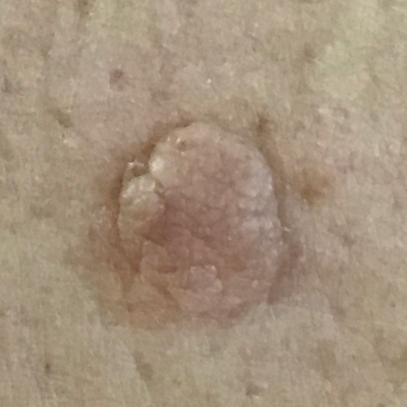imaging: smartphone clinical photo | subject: 61 years old | region: the back | reported symptoms: elevation / no itching, no pain | diagnosis: nevus (clinical consensus).